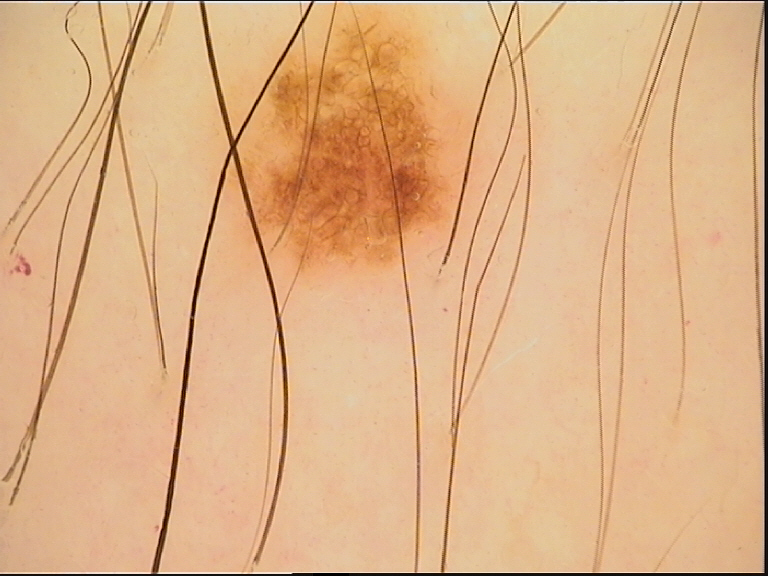A dermoscopic image of a skin lesion.
Diagnosed as a dysplastic junctional nevus.